The photograph was taken at a distance; the contributor is 60–69, female; present for about one day; the lesion is associated with burning, pain and itching; the lesion involves the arm; the patient considered this a rash:
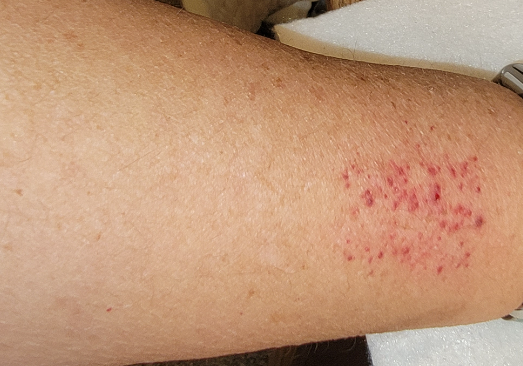Findings:
* impression — Contact purpura (considered); Purpura (considered); Vasculitis of the skin, NOS (less likely)